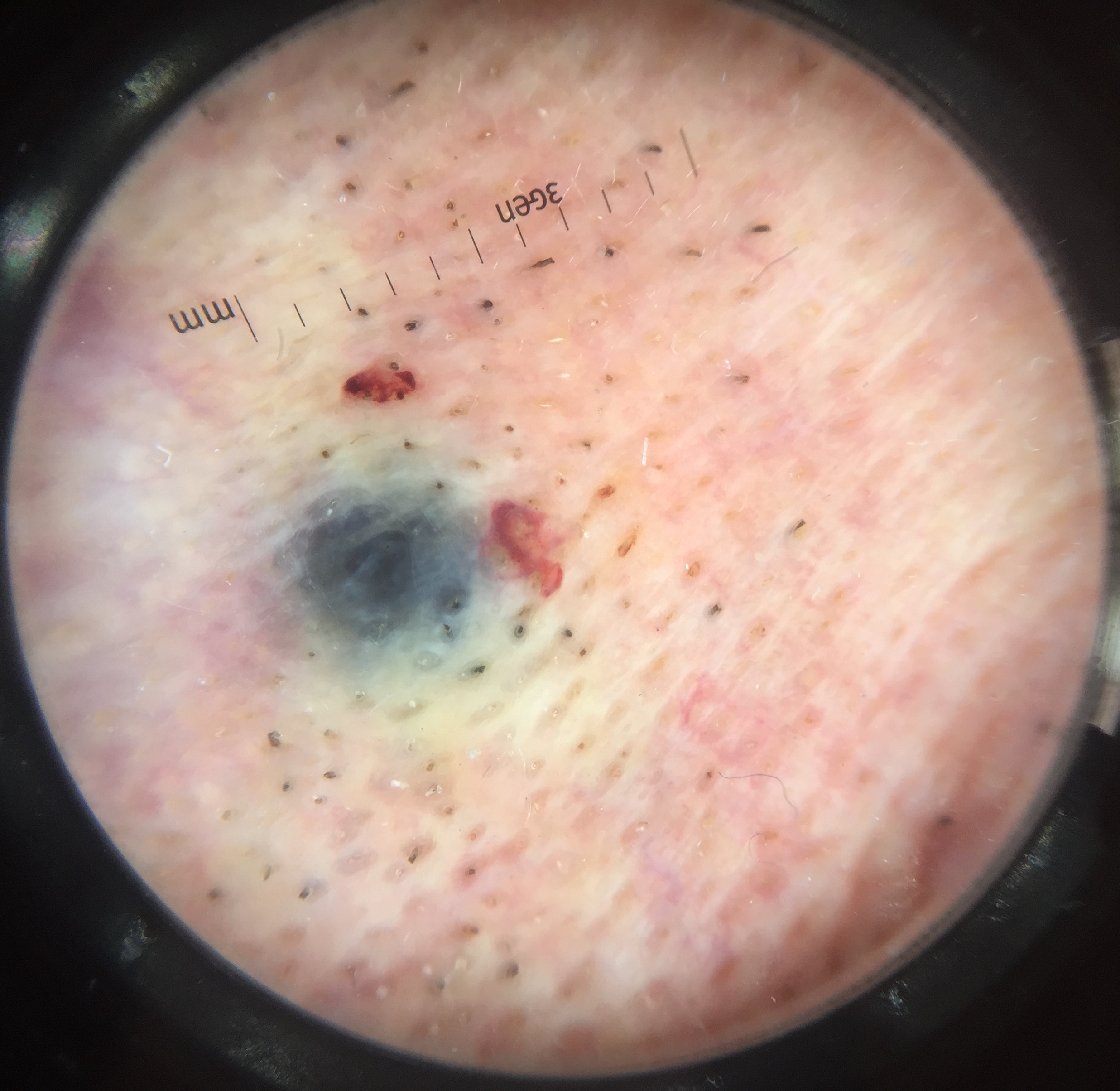The diagnosis was a blue nevus.